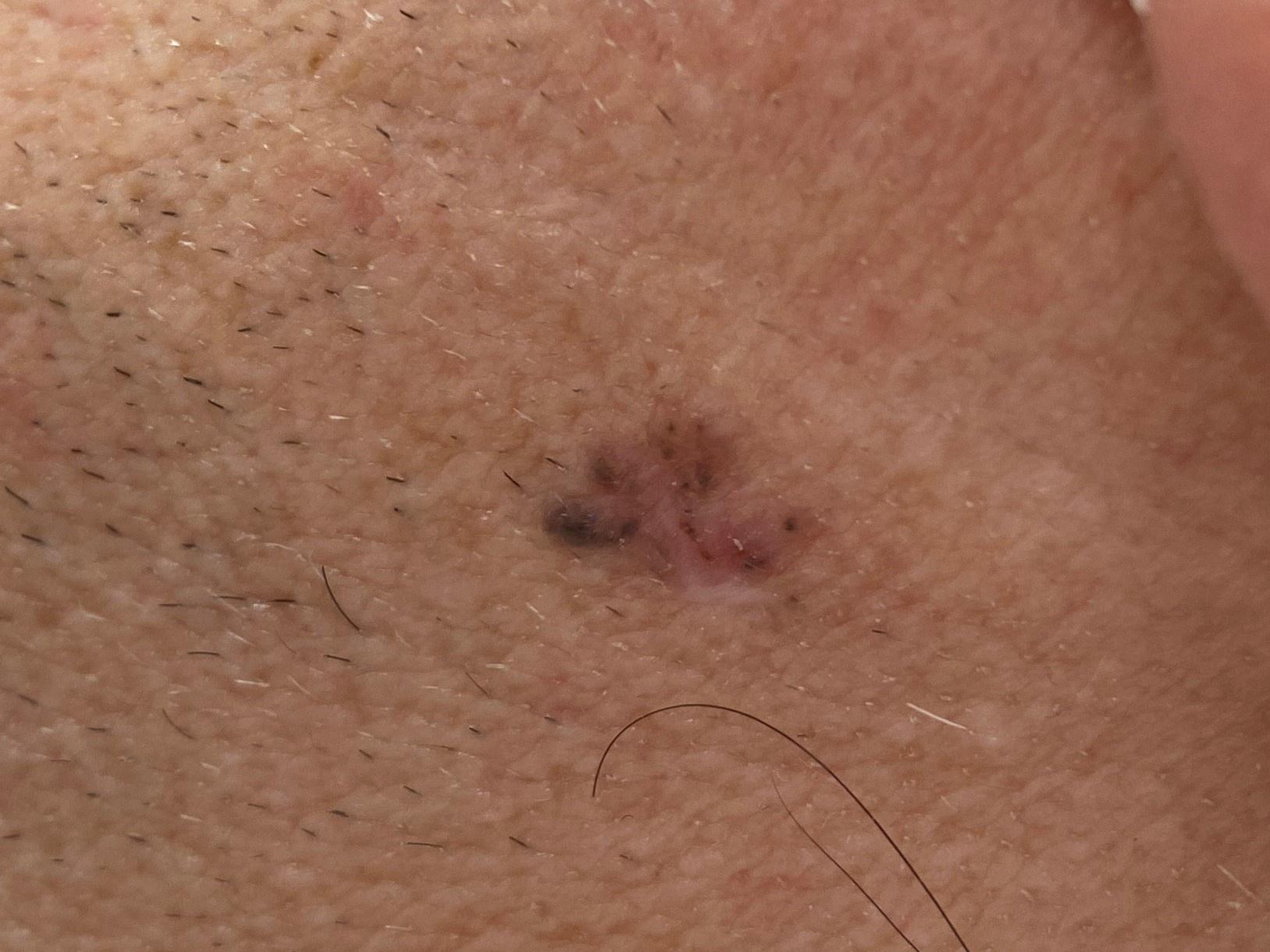diagnosis:
  name: Basal cell carcinoma
  malignancy: malignant
  confirmation: histopathology
  lineage: adnexal